A female patient roughly 65 years of age. A dermoscopy image of a single skin lesion:
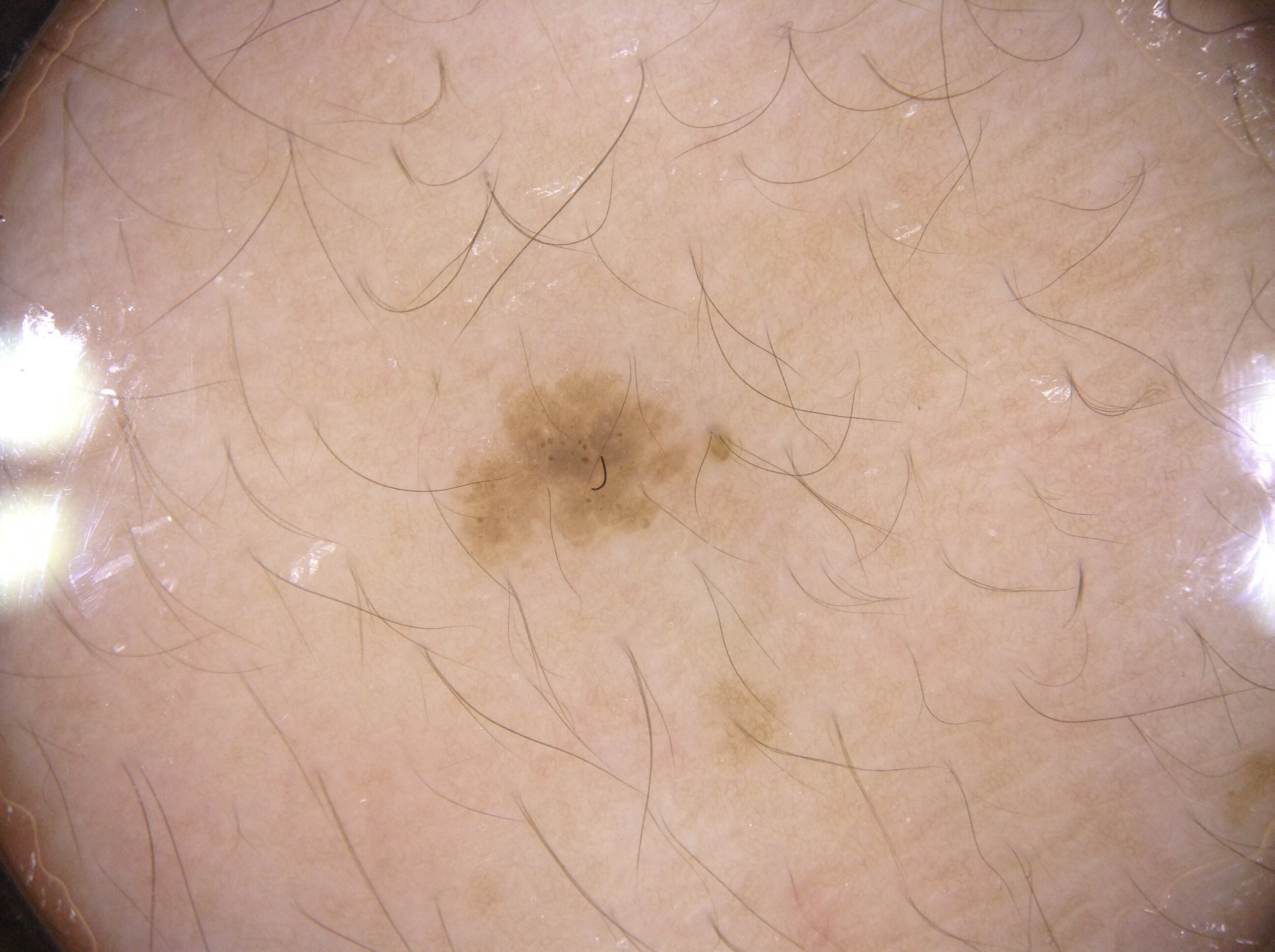Q: Where is the lesion in the image?
A: box(478, 380, 677, 528)
Q: What does dermoscopy show?
A: milia-like cysts; absent: negative network, streaks, and pigment network
Q: How much of the field does the lesion occupy?
A: ~2% of the field
Q: What did the assessment conclude?
A: a seborrheic keratosis, a lesion of keratinocytic origin